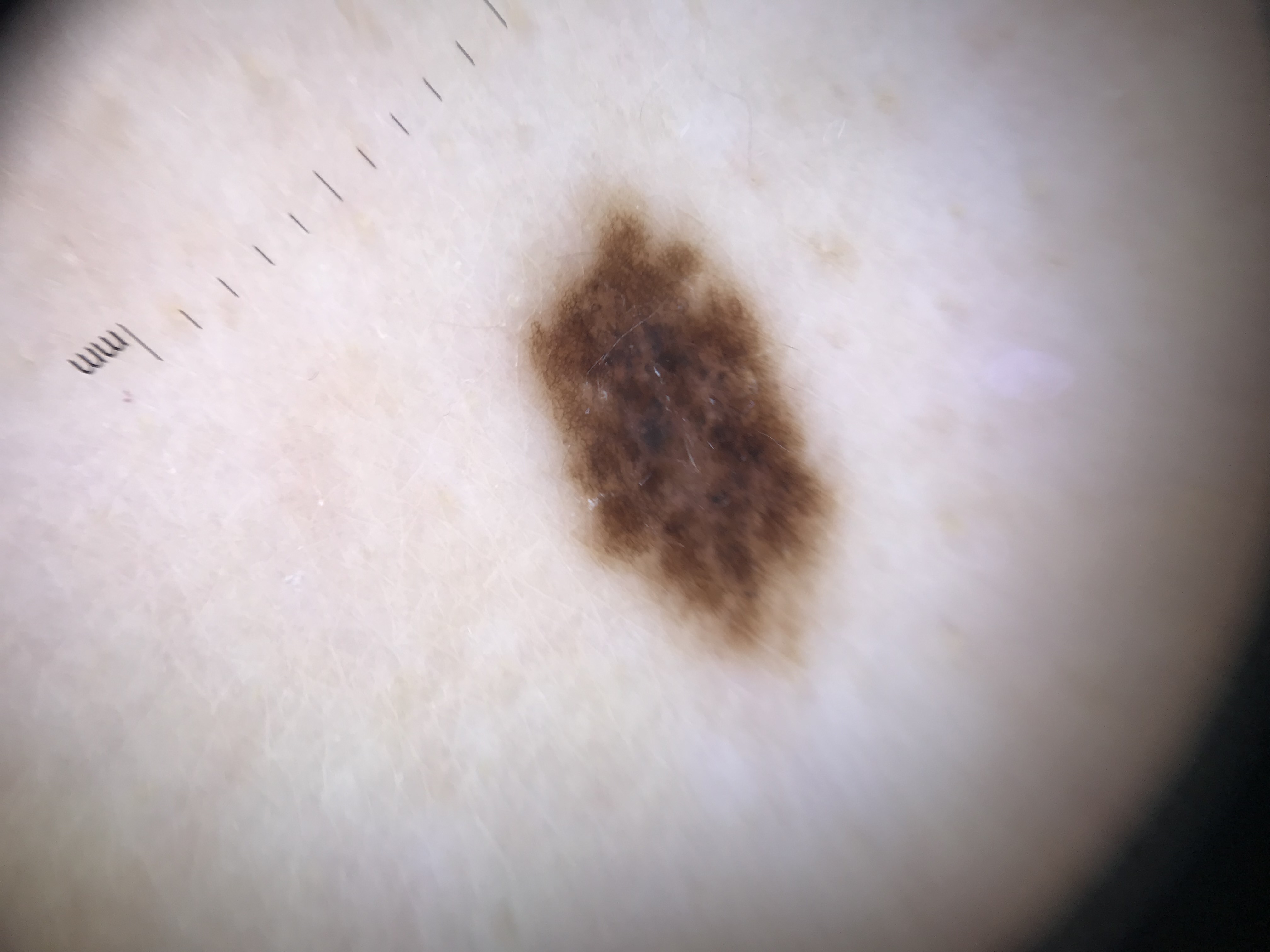imaging: dermatoscopy; diagnostic label: congenital compound nevus (expert consensus).